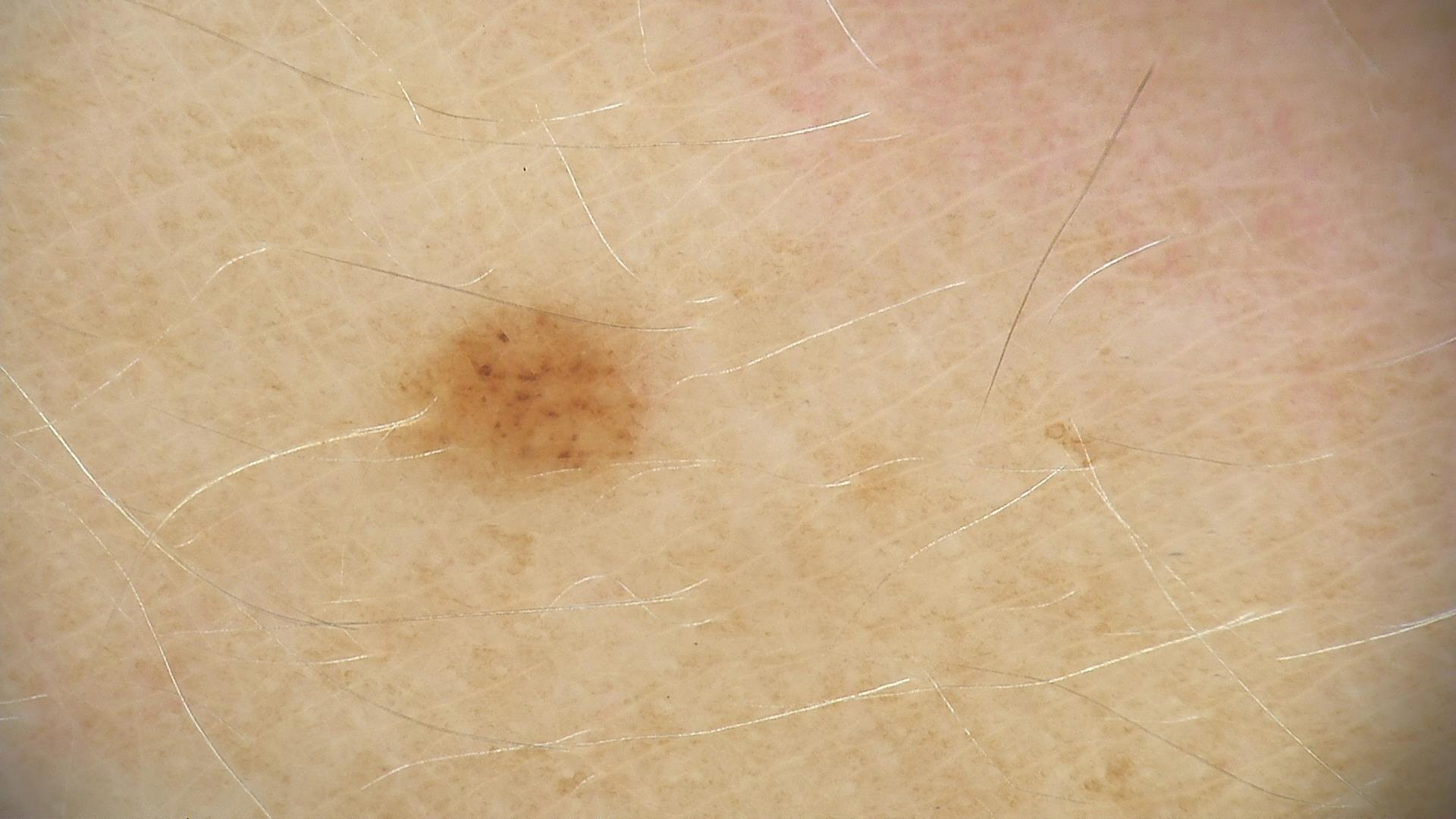Dermoscopy of a skin lesion. Diagnosed as a benign lesion — a dysplastic junctional nevus.